A female subject, in their 70s. Dermoscopy of a skin lesion: 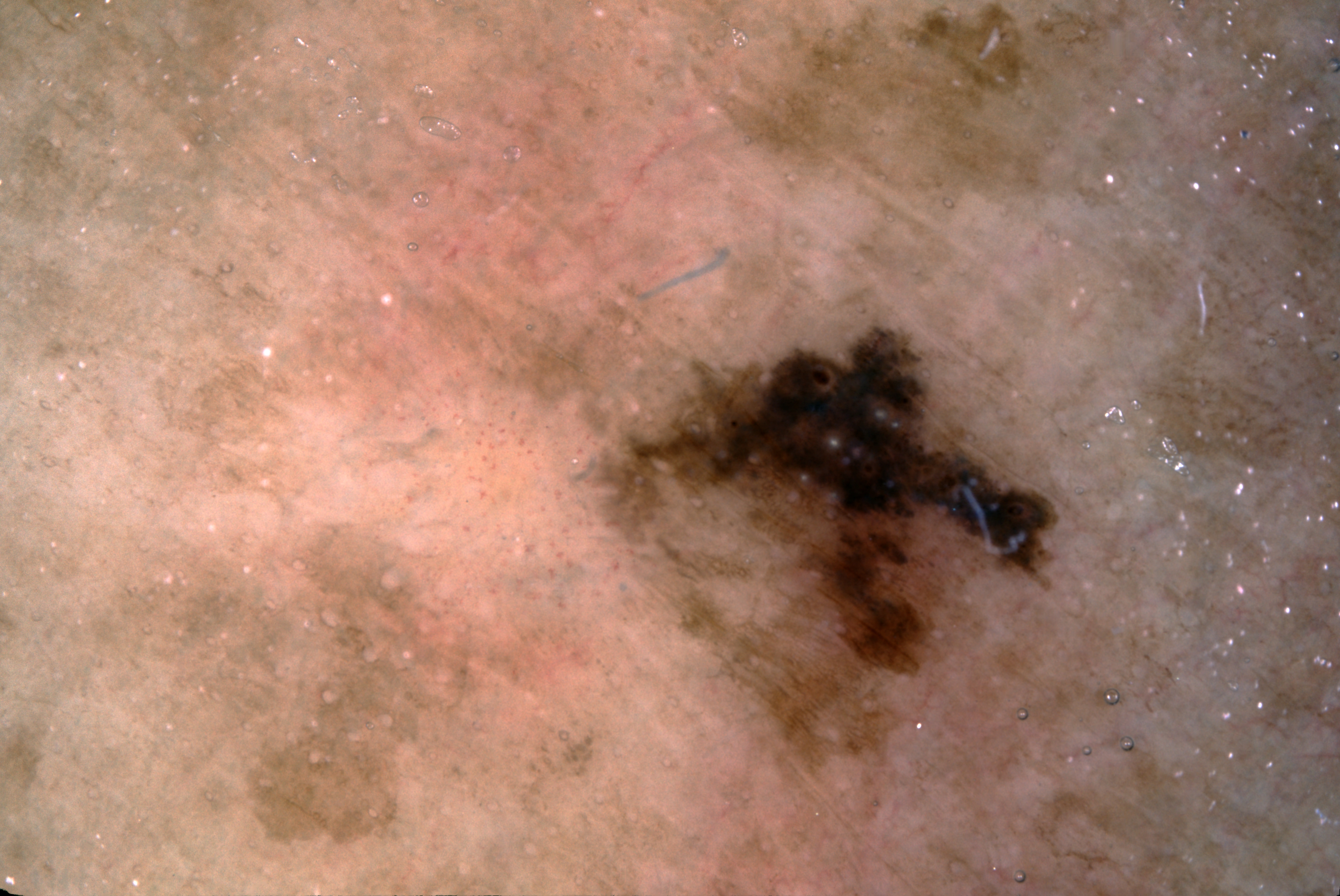| feature | finding |
|---|---|
| dermoscopic pattern | milia-like cysts and pigment network |
| lesion location | x1=579, y1=322, x2=1057, y2=773 |
| diagnostic label | a seborrheic keratosis |